A male patient aged approximately 30; a dermatoscopic image of a skin lesion — 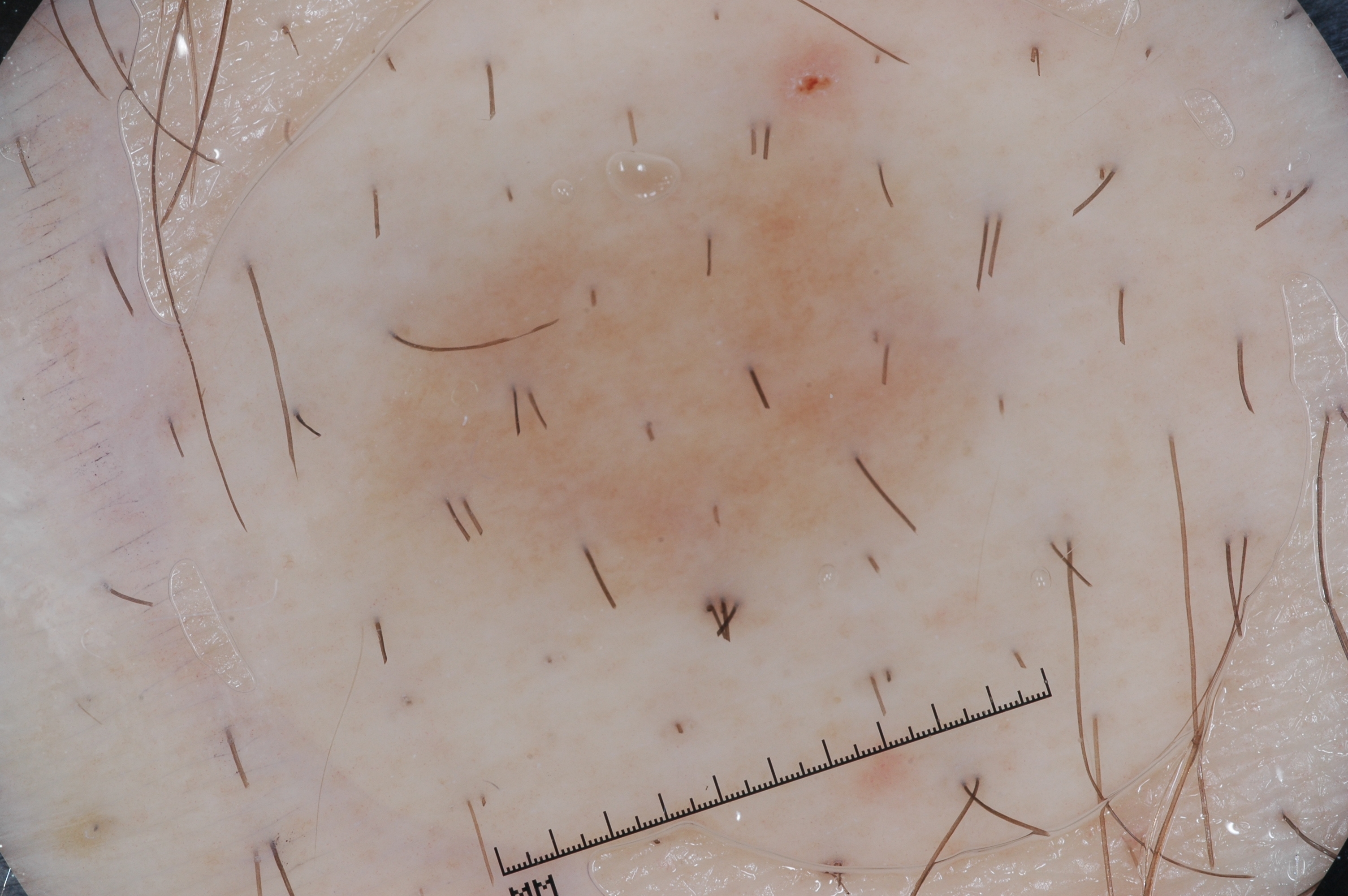The lesion is located at box(302, 22, 1025, 654).
A mid-sized lesion within the field.
Dermoscopically, the lesion shows no milia-like cysts, streaks, negative network, or pigment network.
Consistent with a melanocytic nevus.